The contributor is male, the affected area is the back of the torso, this is a close-up image, Fitzpatrick skin type III; lay graders estimated 3 on the Monk Skin Tone, present for less than one week, texture is reported as raised or bumpy, the patient considered this a rash: 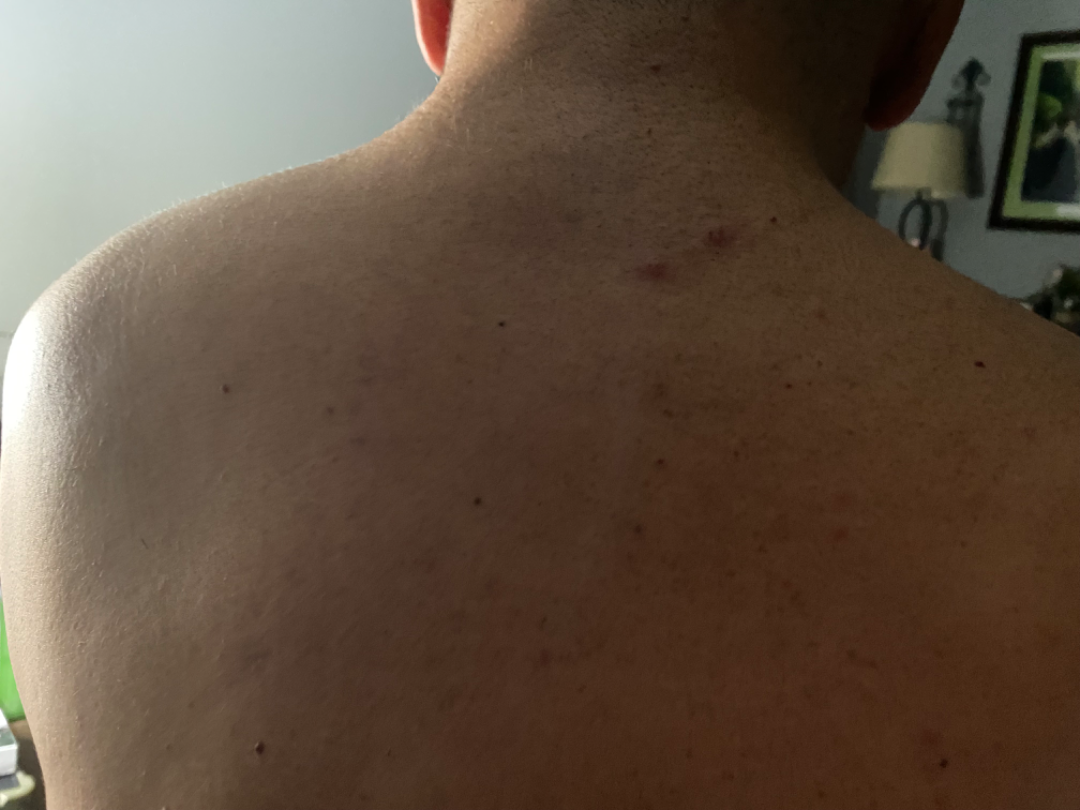Notes:
- assessment: Drug Rash, Eczema and Hypersensitivity were considered with similar weight